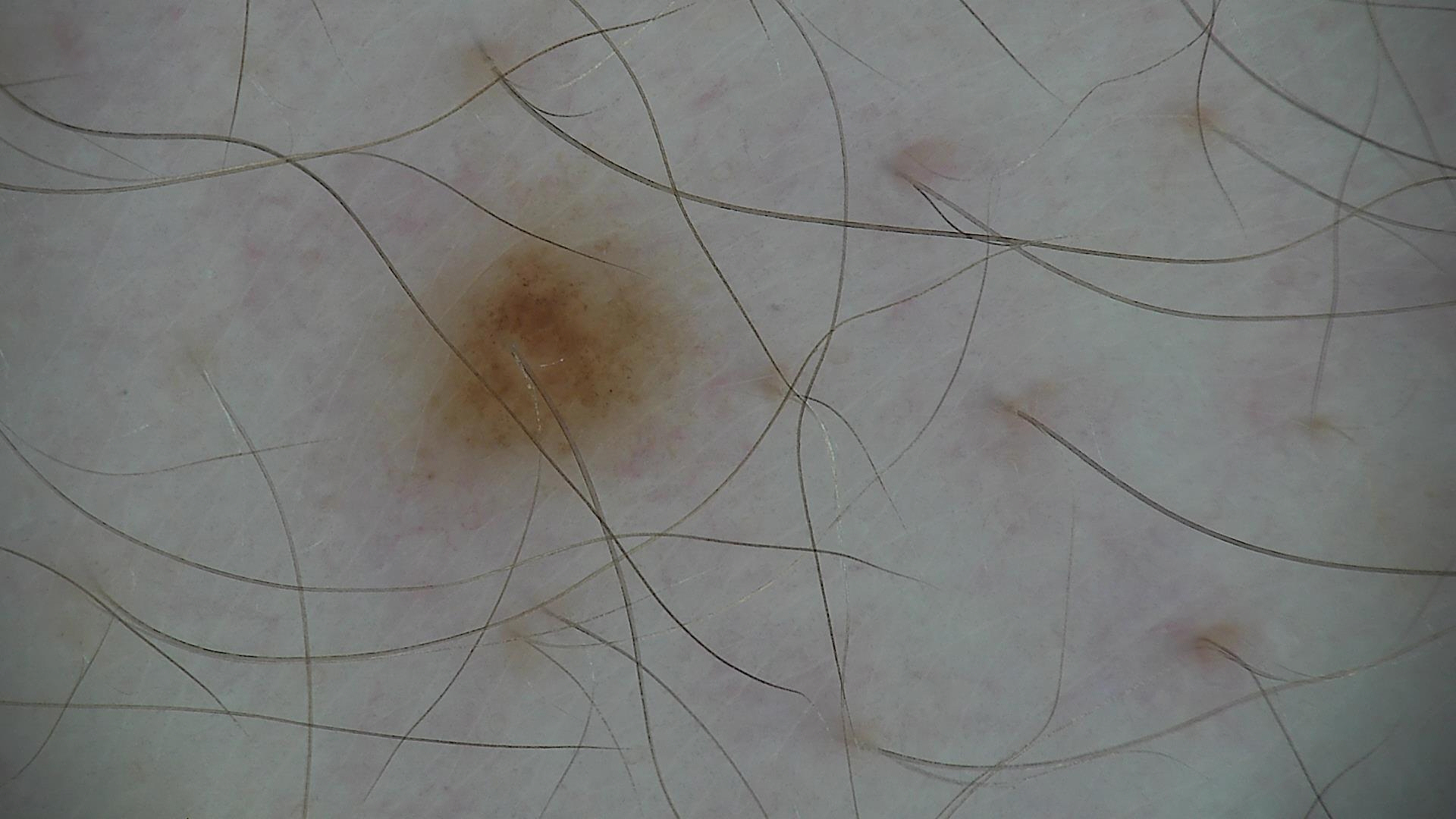image type: dermatoscopy | class: dysplastic junctional nevus (expert consensus).